Close-up view — 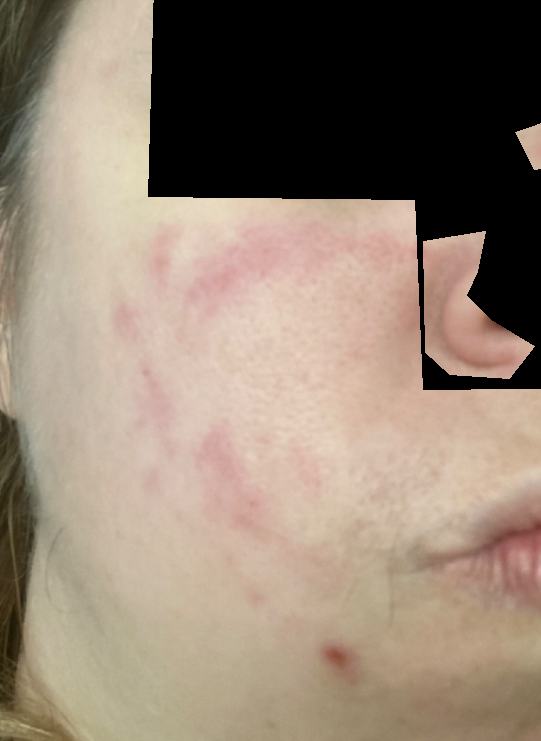| field | value |
|---|---|
| skin tone | lay reviewers estimated Monk Skin Tone 2 (US pool) or 3 (India pool) |
| onset | less than one week |
| patient-reported symptoms | bothersome appearance, itching and burning |
| patient's own categorization | a rash |
| lesion texture | raised or bumpy |
| dermatologist impression | most consistent with Rosacea |